This is a dermoscopic photograph of a skin lesion.
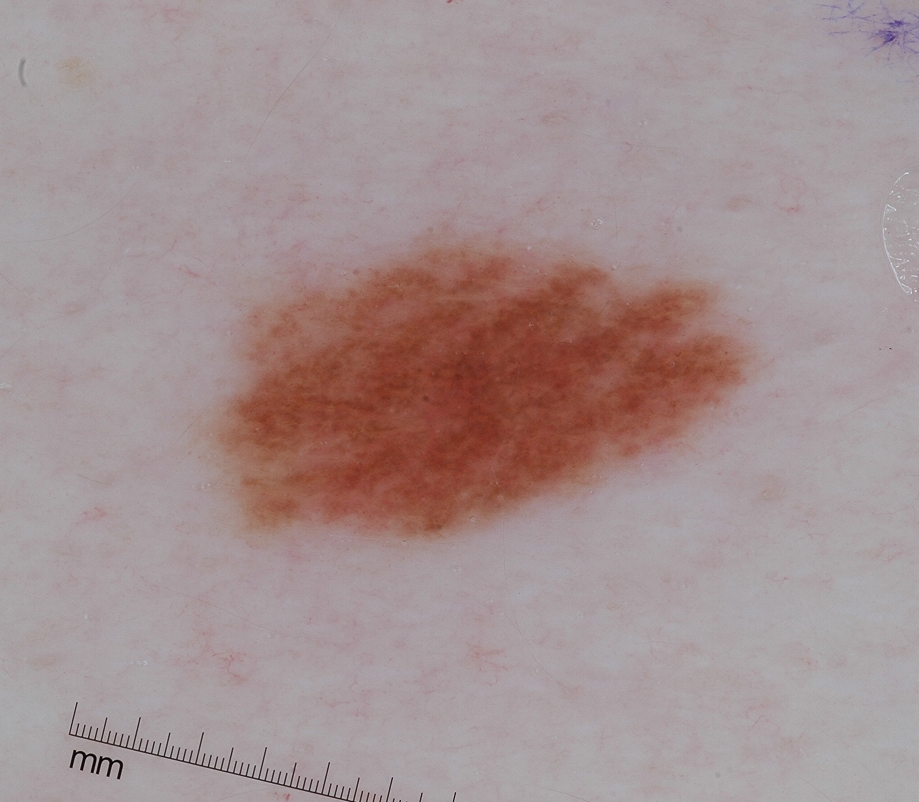The lesion takes up a moderate portion of the field.
The lesion spans left=203, top=225, right=750, bottom=540.
Dermoscopic examination shows globules.
Consistent with a melanocytic nevus.